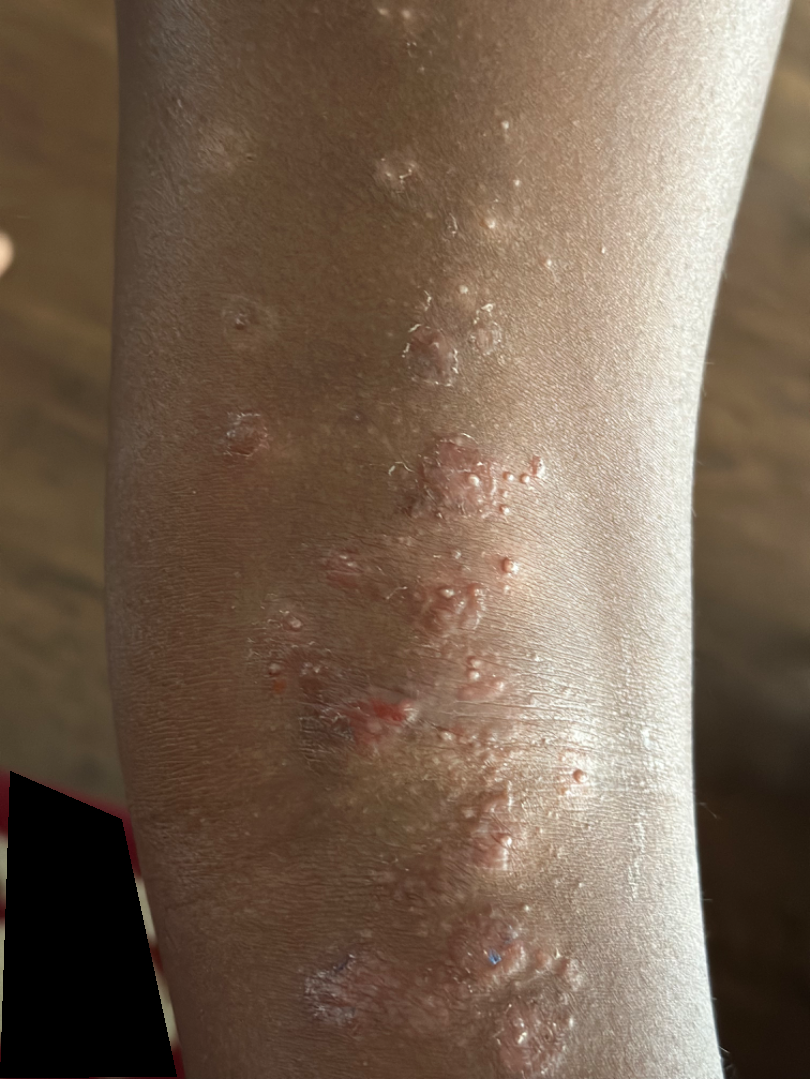The condition could not be reliably identified from the image. A close-up photograph. Texture is reported as fluid-filled and raised or bumpy. Skin tone: Fitzpatrick phototype VI. The patient considered this a rash. The patient notes itching, burning, bothersome appearance and enlargement. The affected area is the leg. The condition has been present for three to twelve months.